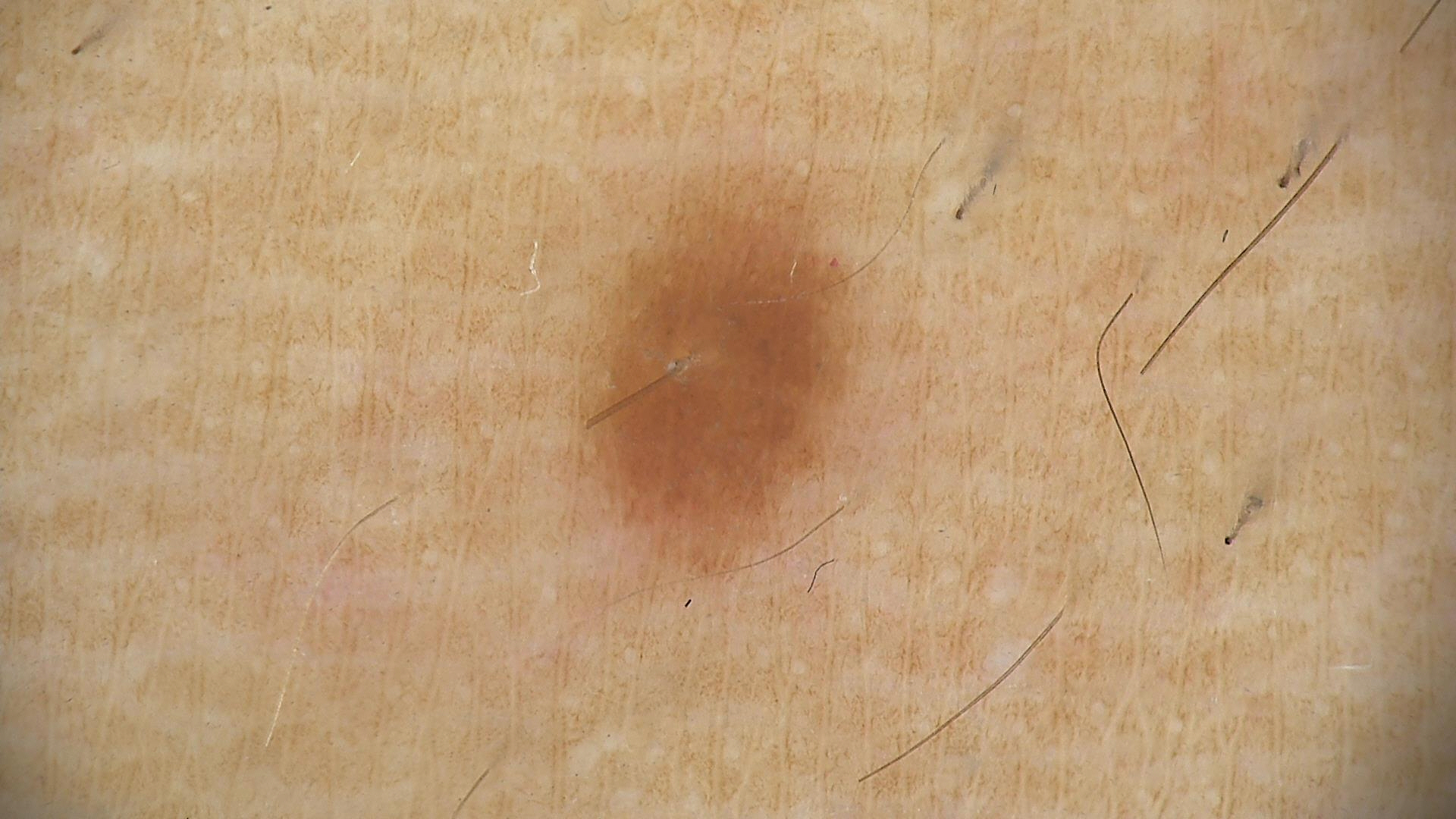Findings: A dermoscopic image of a skin lesion. Impression: Consistent with a dysplastic junctional nevus.